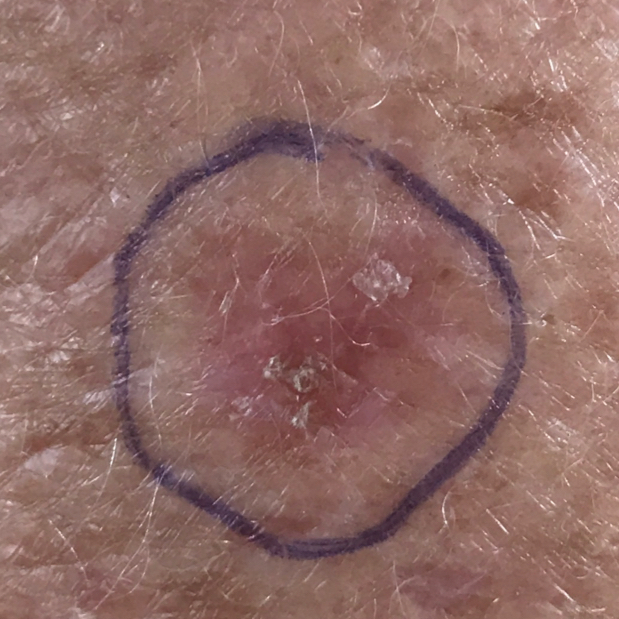A clinical photo of a skin lesion taken with a smartphone. Skin type II. No symptoms reported. Histopathologically confirmed as a lesion of indeterminate malignant potential — an actinic keratosis.